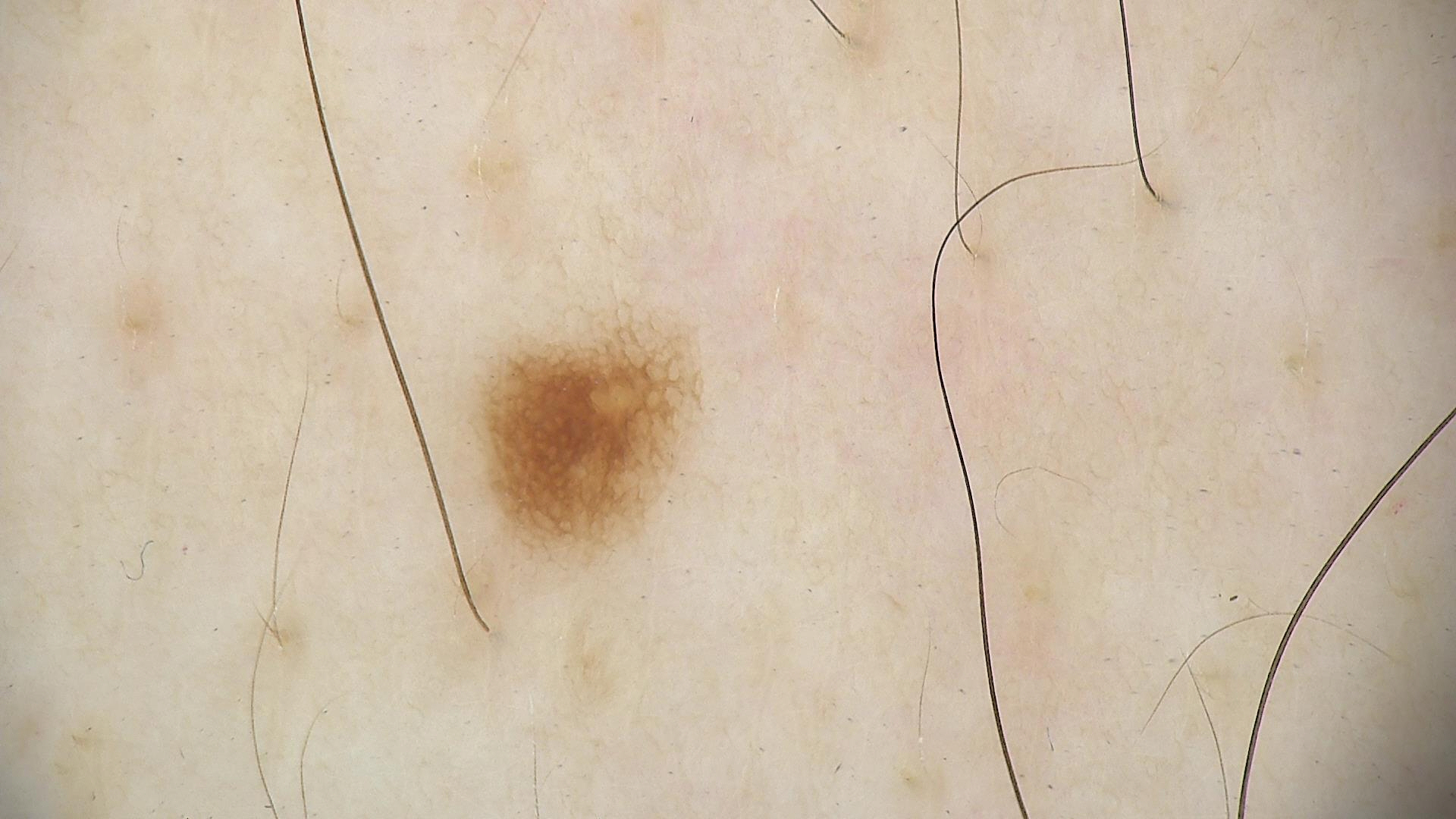Q: What was the diagnostic impression?
A: dysplastic junctional nevus (expert consensus)